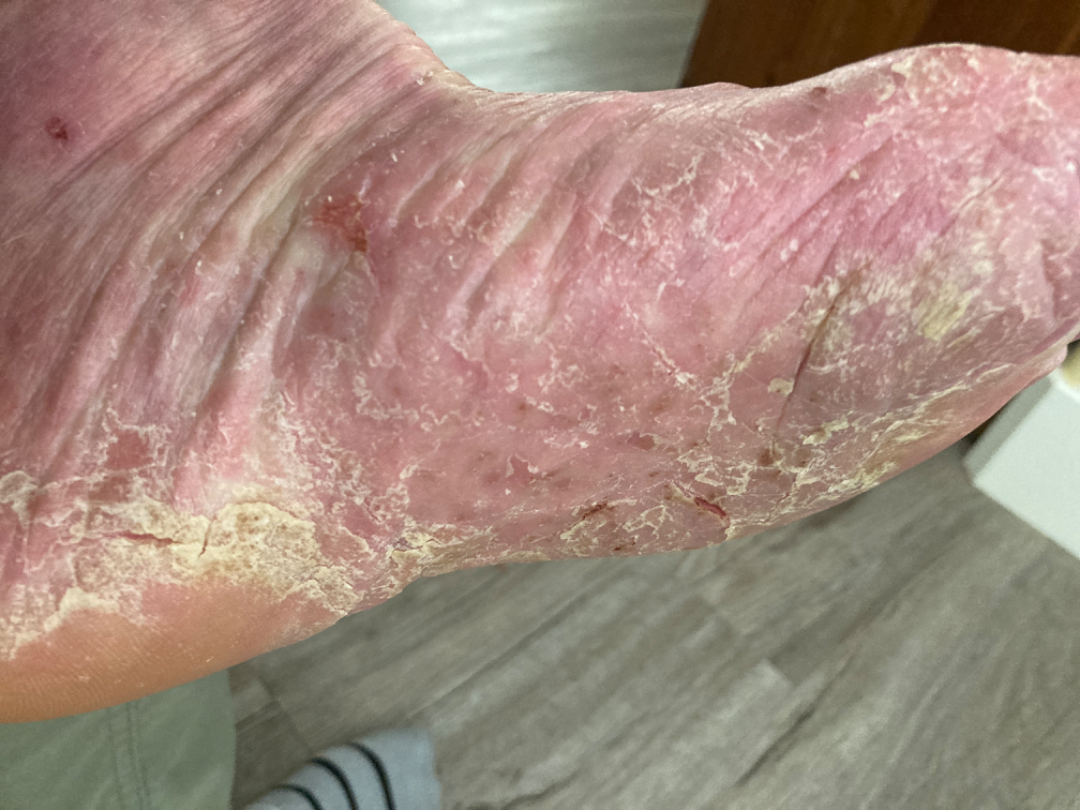differential diagnosis: Psoriasis and Eczema were each considered, in no particular order; less probable is Tinea